Dermoscopy of a skin lesion; a male patient, aged 58 to 62.
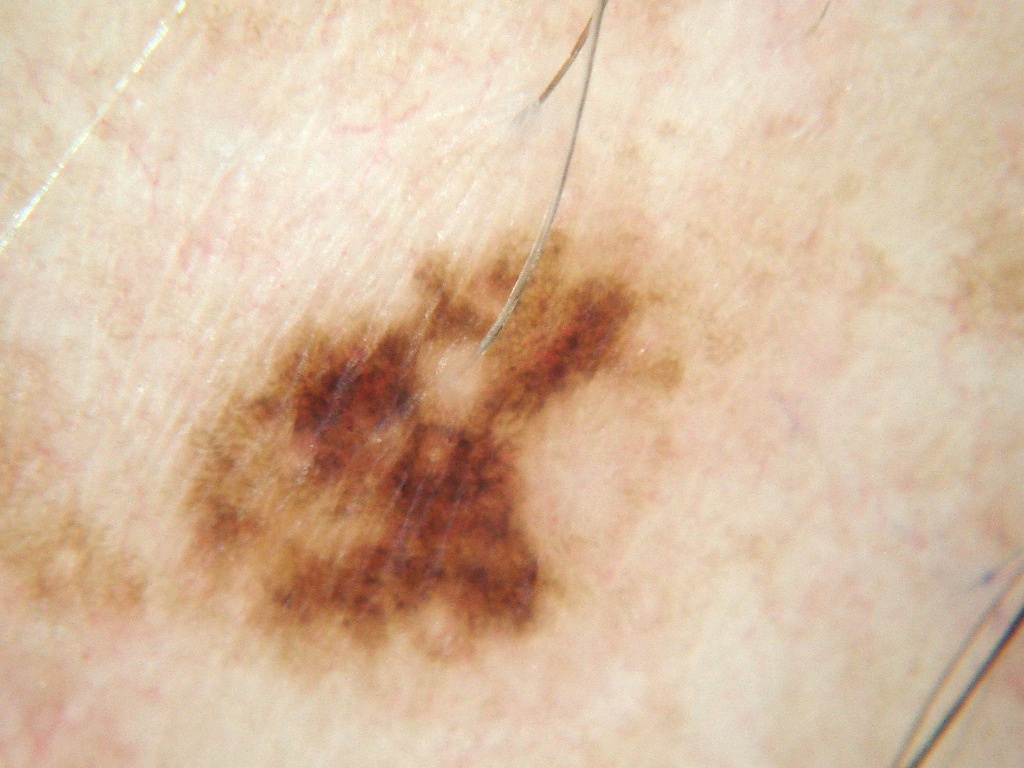Q: What is the lesion's bounding box?
A: box(176, 228, 682, 669)
Q: What dermoscopic features are present?
A: pigment network and globules
Q: What is this lesion?
A: a melanocytic nevus, a benign lesion